A female patient 60 years old. A dermoscopy image of a skin lesion. The patient says their skin tans without first burning. Referred for assessment of suspected basal cell carcinoma:
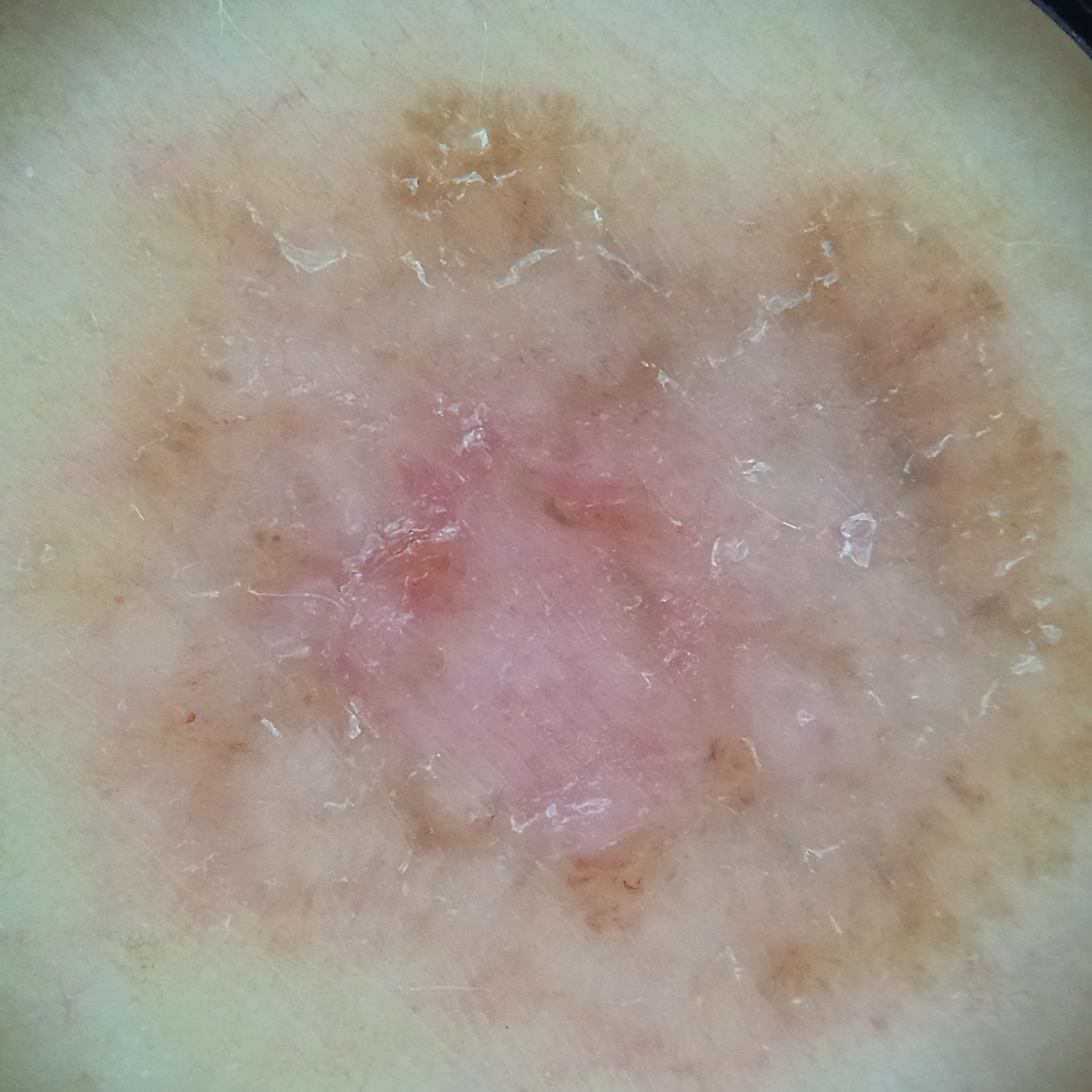diameter: 13.2 mm; diagnosis: basal cell carcinoma (dermatologist consensus).